A dermoscopic image of a skin lesion: 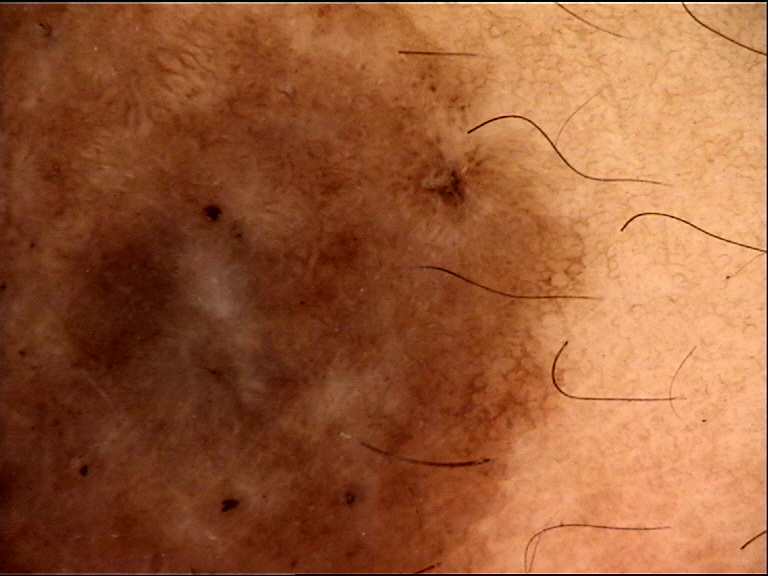Findings:
– category: banal
– diagnosis: congenital compound nevus (expert consensus)